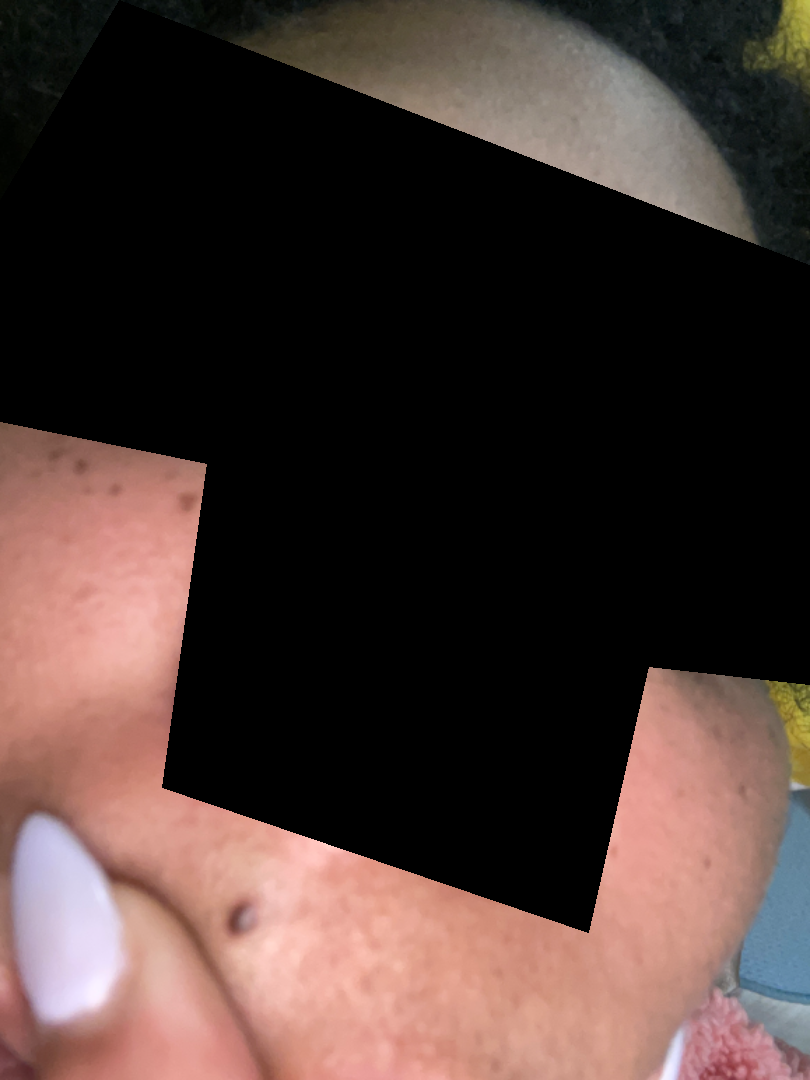Review: No skin condition was discernible on photographic review. Patient information: Fitzpatrick skin type V. The lesion involves the head or neck. Texture is reported as raised or bumpy and rough or flaky. The patient also reports fatigue. Reported lesion symptoms include bothersome appearance, pain and itching. The photo was captured at a distance.